Imaged for a research study, with no referral diagnosis recorded. A male subject aged 73. A clinical photograph showing a skin lesion:
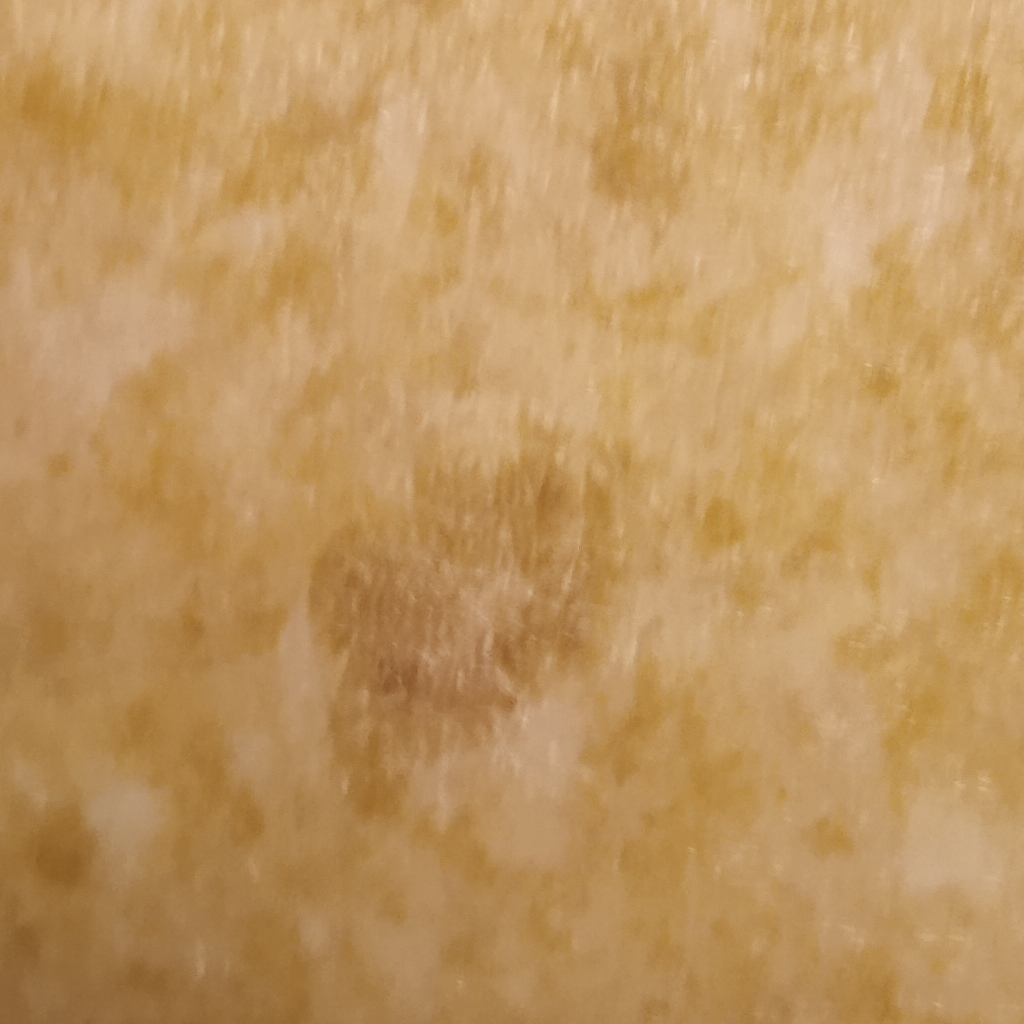– anatomic site — the back
– size — 10.7 mm
– diagnosis — seborrheic keratosis (dermatologist consensus)